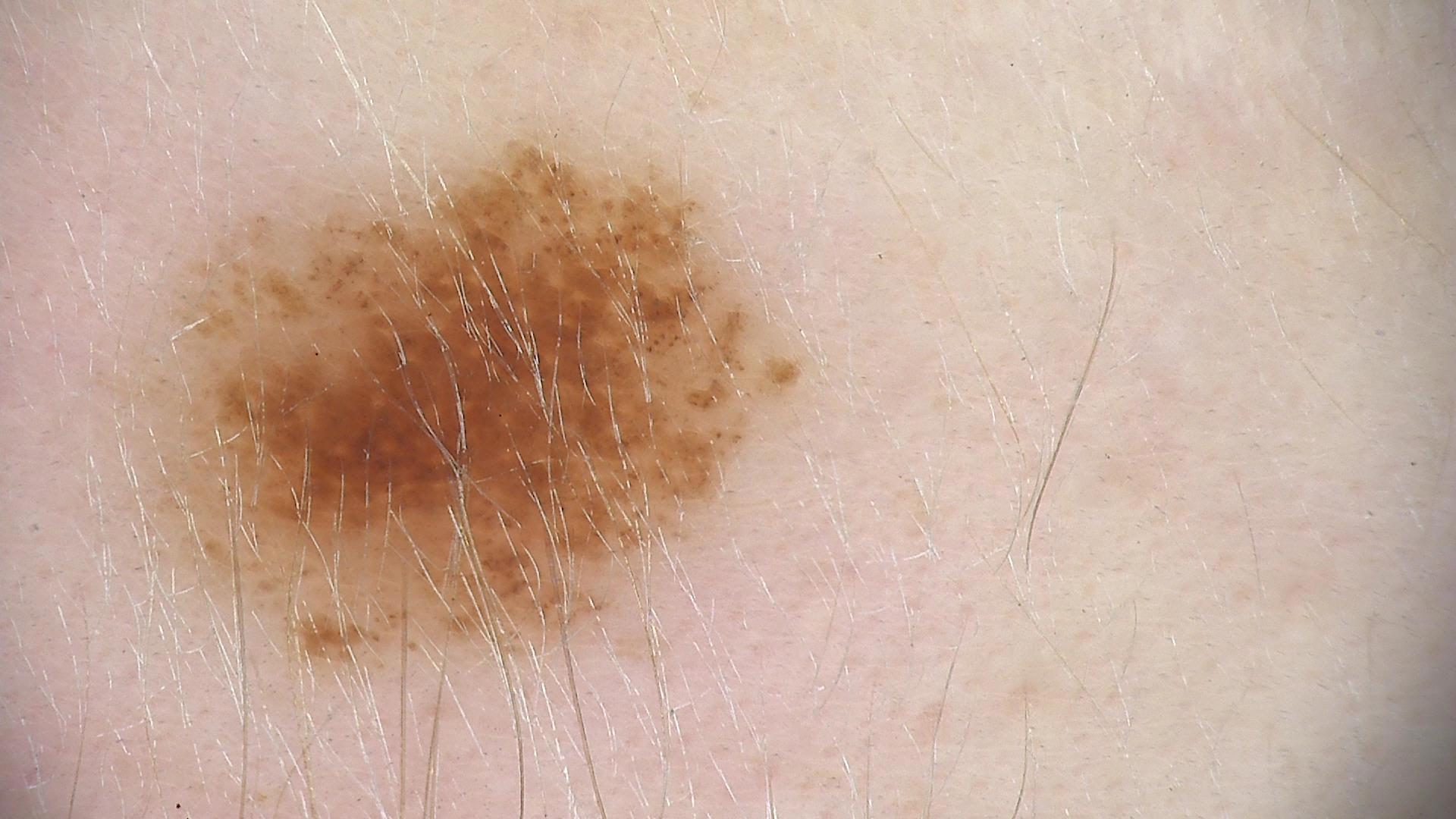<dermoscopy>
<image>dermoscopy</image>
<diagnosis>
<name>dysplastic junctional nevus</name>
<code>jd</code>
<malignancy>benign</malignancy>
<super_class>melanocytic</super_class>
<confirmation>expert consensus</confirmation>
</diagnosis>
</dermoscopy>